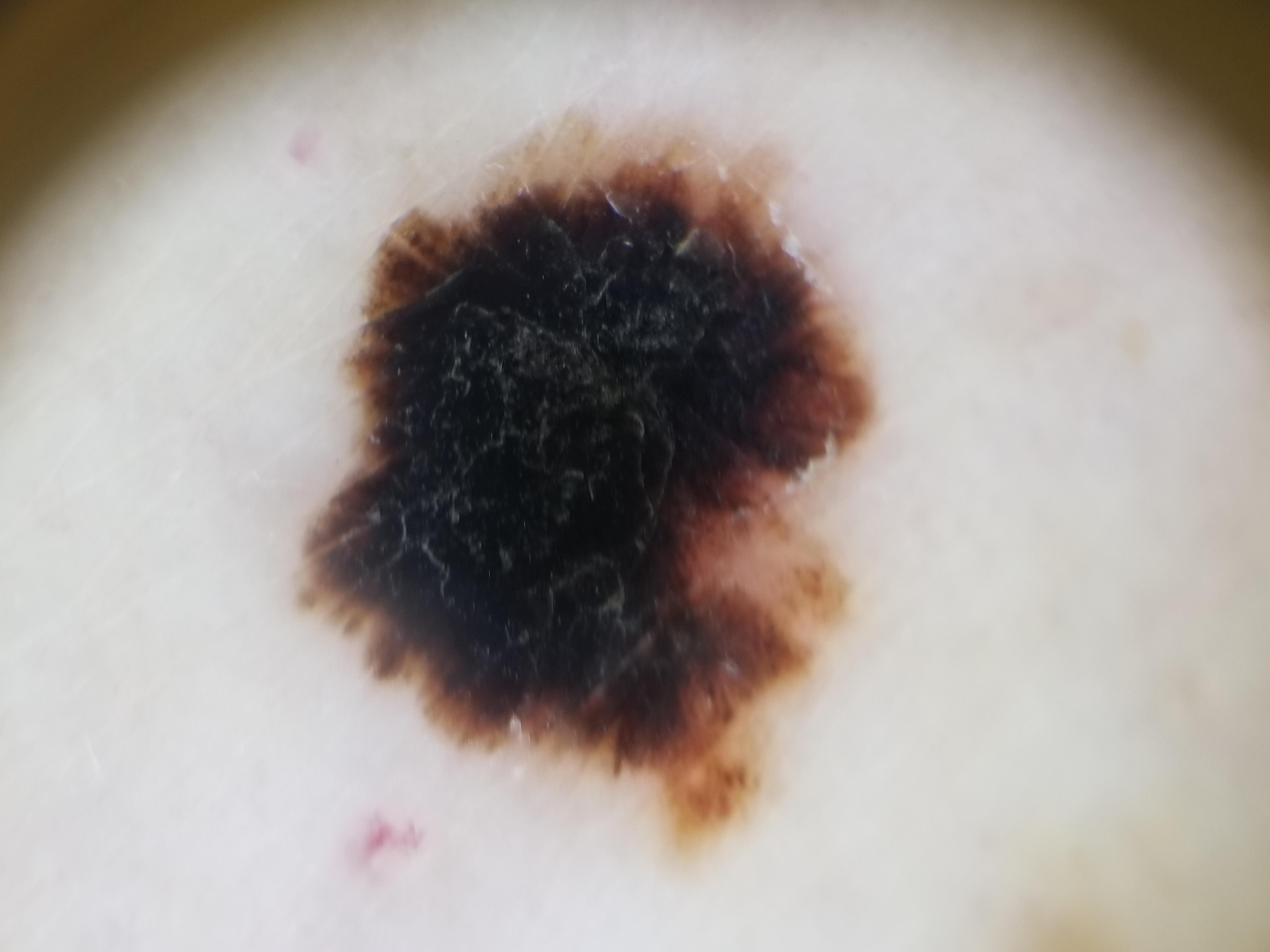Findings: Contact-polarized dermoscopy of a skin lesion. A female patient approximately 85 years of age or older. Conclusion: On biopsy, the diagnosis was a melanoma.